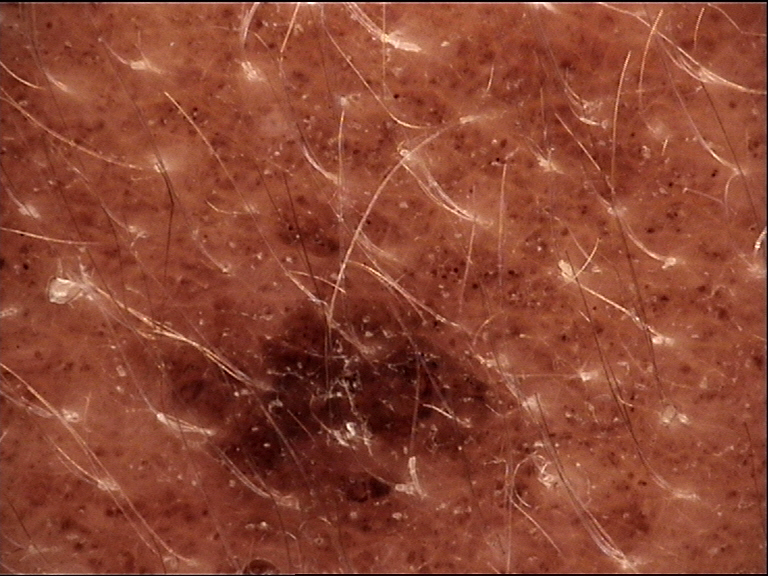The architecture is that of a banal lesion.
Diagnosed as a congenital compound nevus.